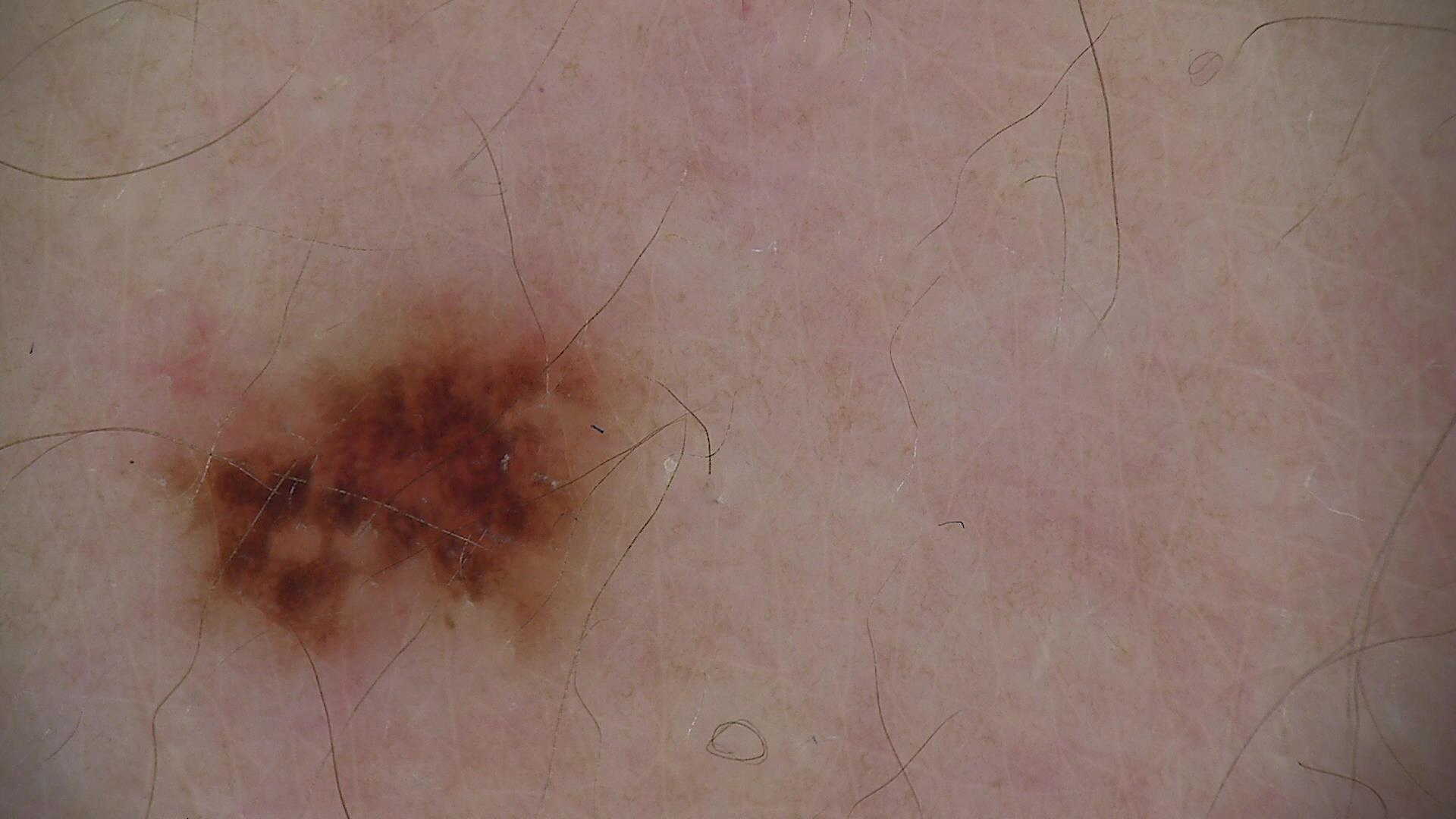* diagnostic label · dysplastic compound nevus (expert consensus)